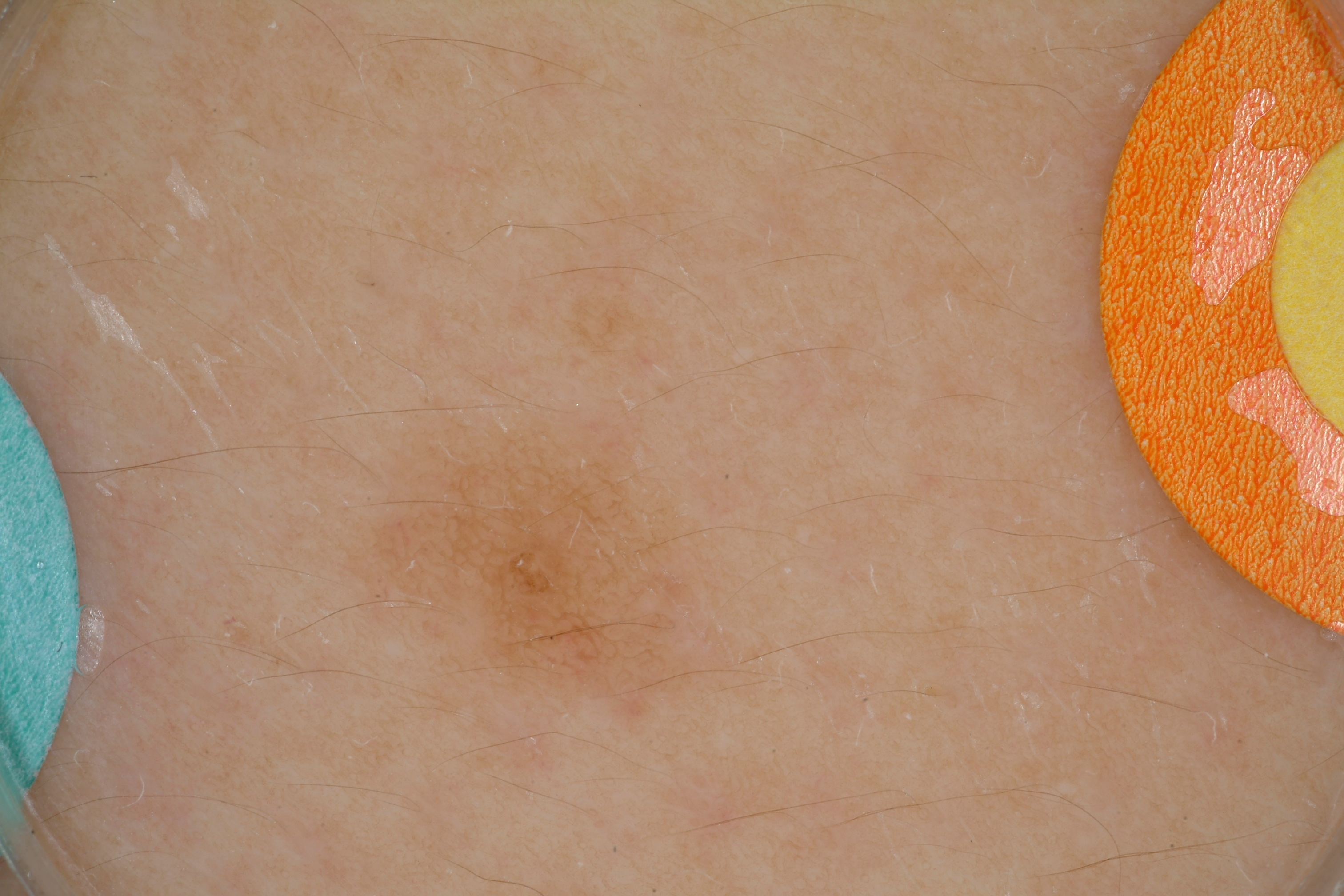Case summary:
A male patient, aged 13 to 17. Dermoscopy of a skin lesion. Dermoscopically, the lesion shows pigment network. With coordinates (x1, y1, x2, y2), lesion location: 370 425 690 695.
Assessment:
Expert review diagnosed this as a melanocytic nevus, a benign lesion.